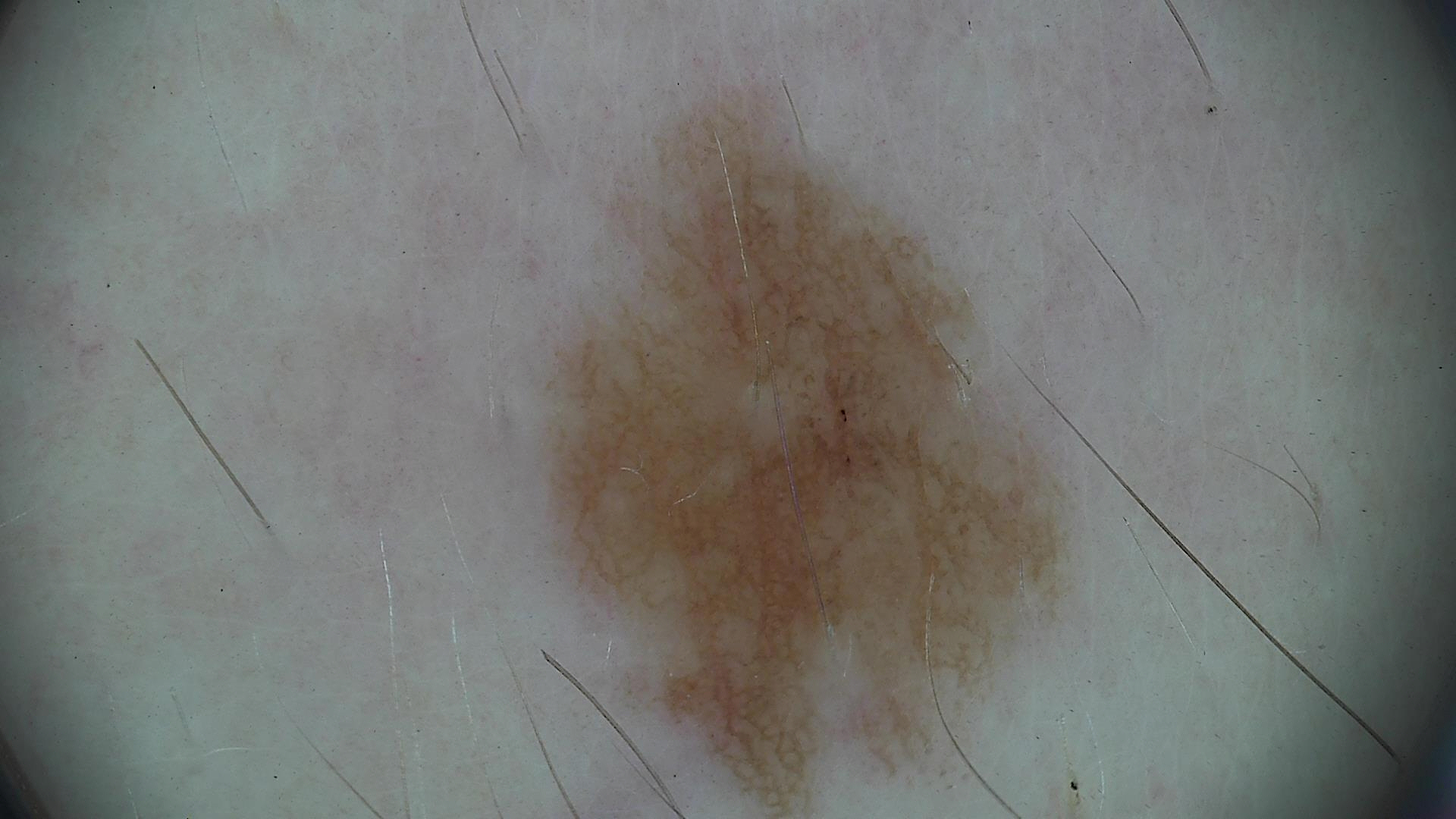| key | value |
|---|---|
| image | dermatoscopy |
| class | dysplastic junctional nevus (expert consensus) |